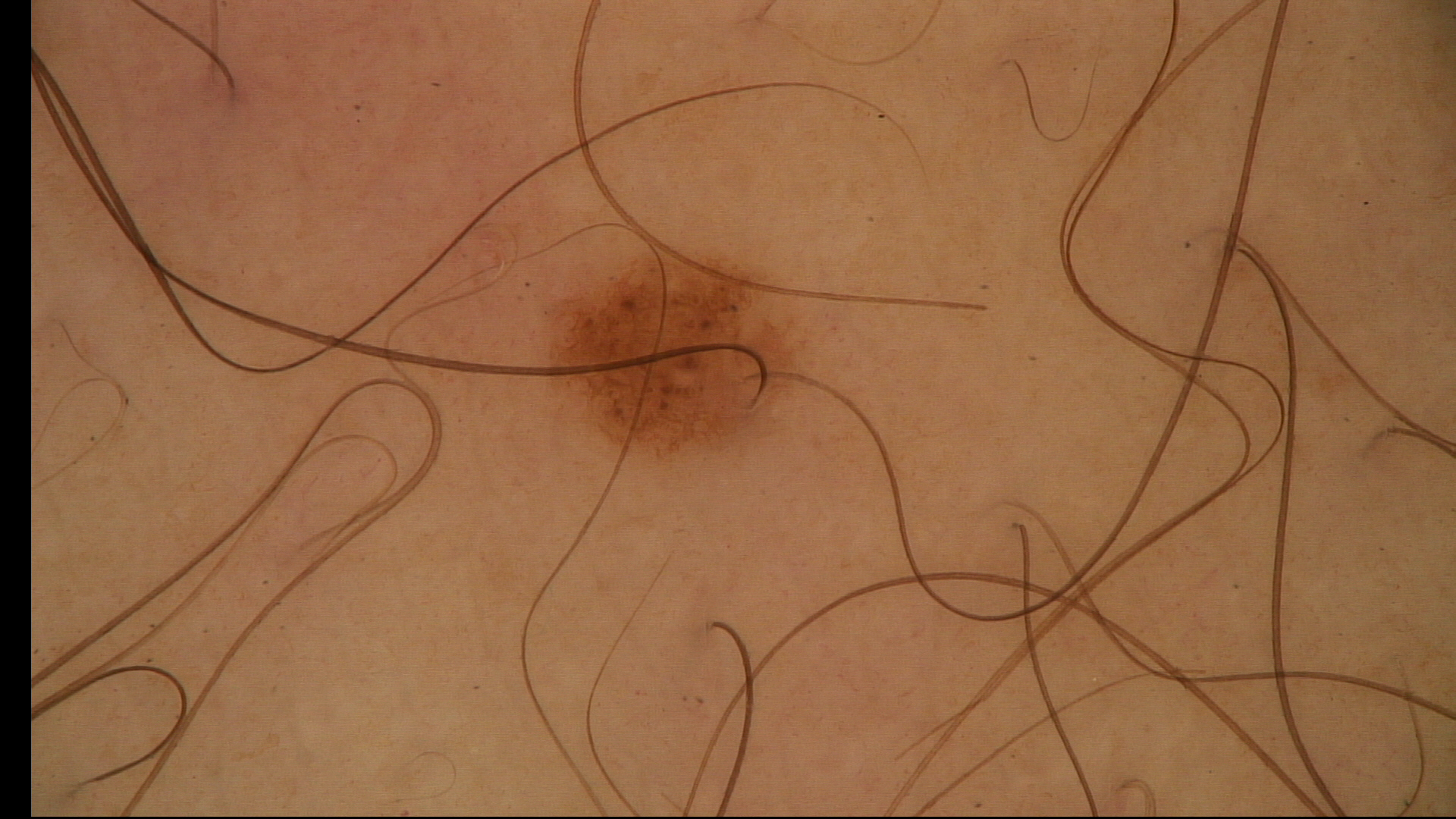lesion type = banal | assessment = junctional nevus (expert consensus).